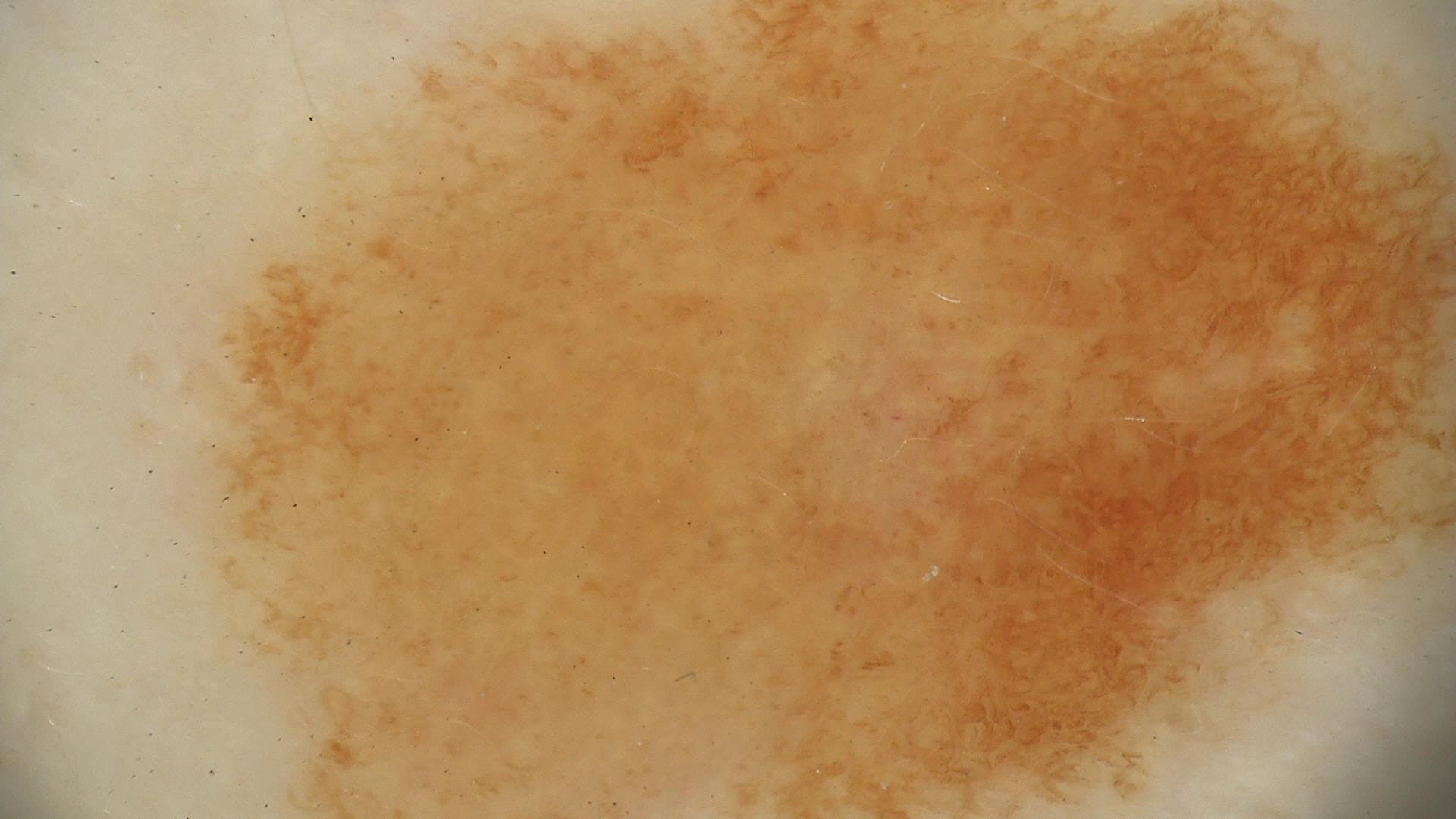Impression:
Consistent with a dysplastic junctional nevus.